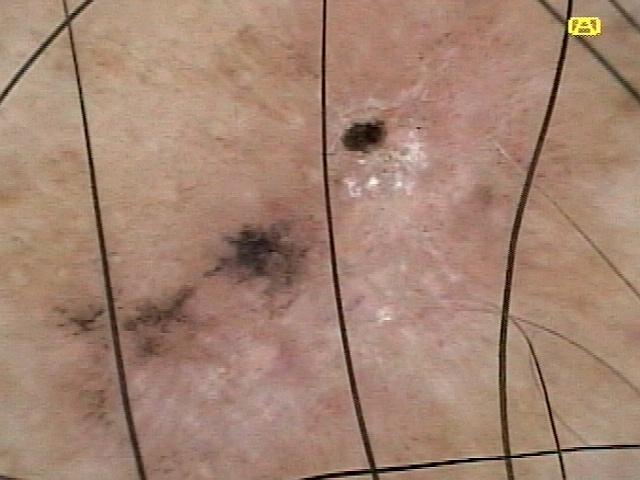A contact-polarized dermoscopy image of a skin lesion. A male subject roughly 55 years of age. The lesion involves the trunk. The biopsy diagnosis was a basal cell carcinoma.